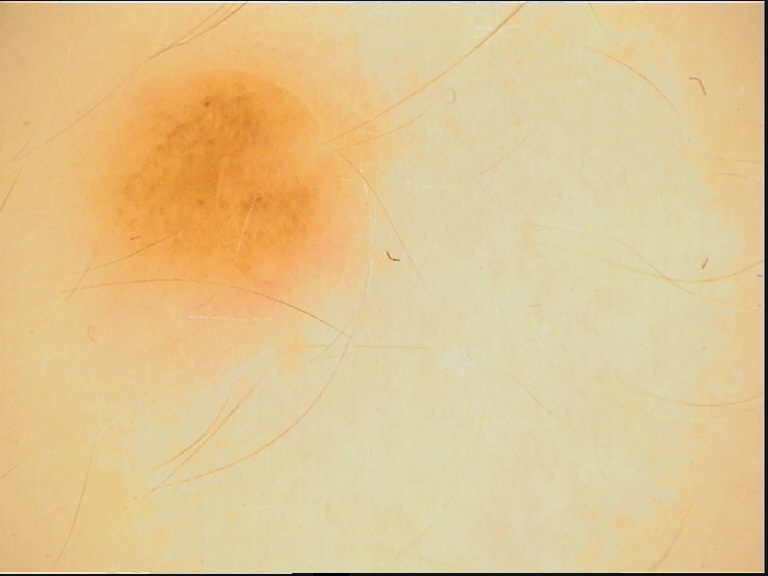Summary:
A dermoscopic image of a skin lesion. The architecture is that of a banal lesion.
Impression:
Labeled as a compound nevus.